An image taken at an angle · self-categorized by the patient as a rash · the patient reports the lesion is raised or bumpy · the affected area is the leg · symptoms reported: burning, bothersome appearance, darkening, itching and enlargement:
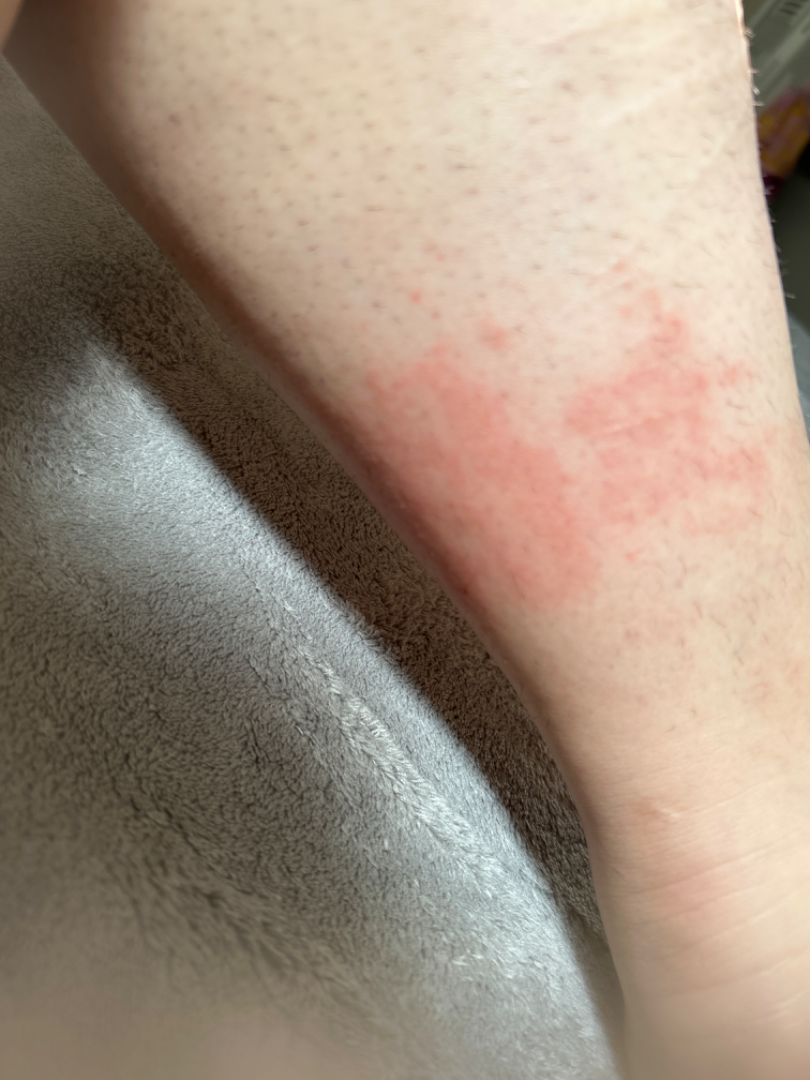The impression was split between Urticaria and Eczema; a more distant consideration is Irritant Contact Dermatitis.